The lesion involves the back of the torso. This image was taken at an angle:
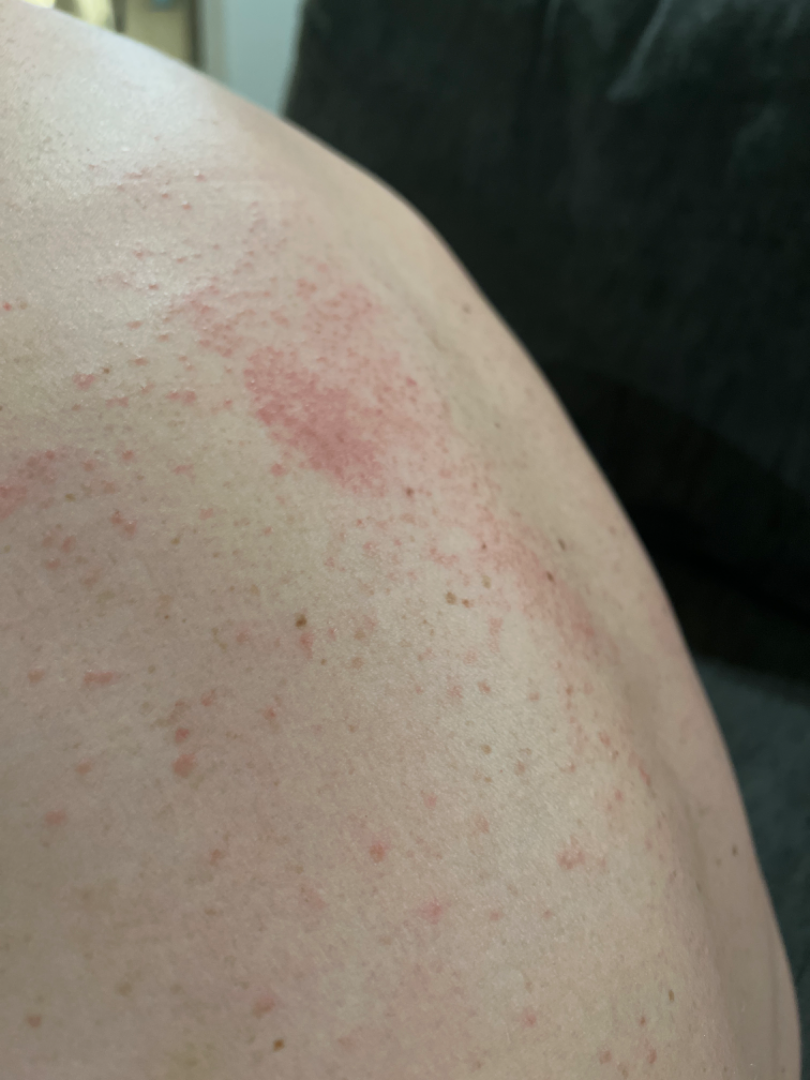diagnostic considerations = reviewed remotely by one dermatologist: Acute dermatitis, NOS and Allergic Contact Dermatitis were considered with similar weight.